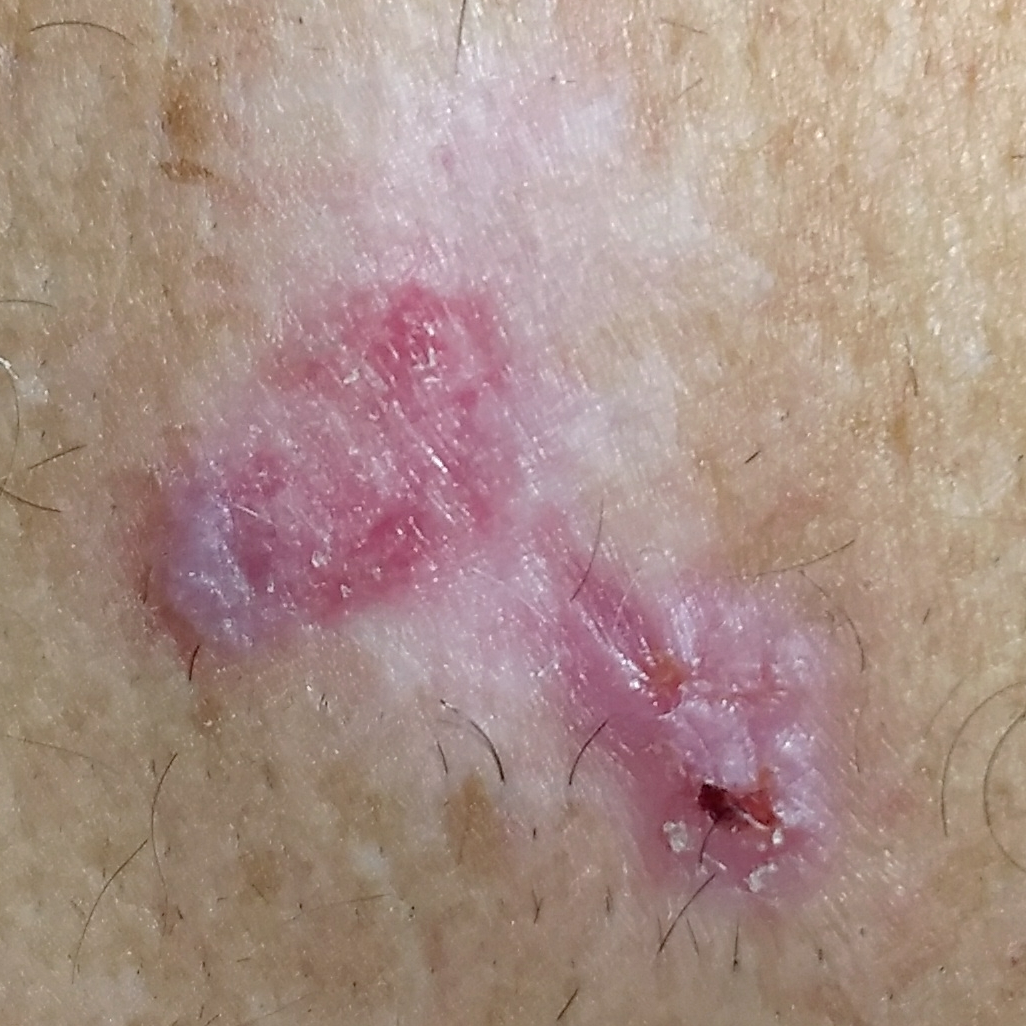Summary: A clinical photograph of a skin lesion. A male subject 71 years old. The lesion is located on the back. Per patient report, the lesion has grown, itches, and has bled, but does not hurt. Diagnosis: Biopsy-confirmed as a basal cell carcinoma.